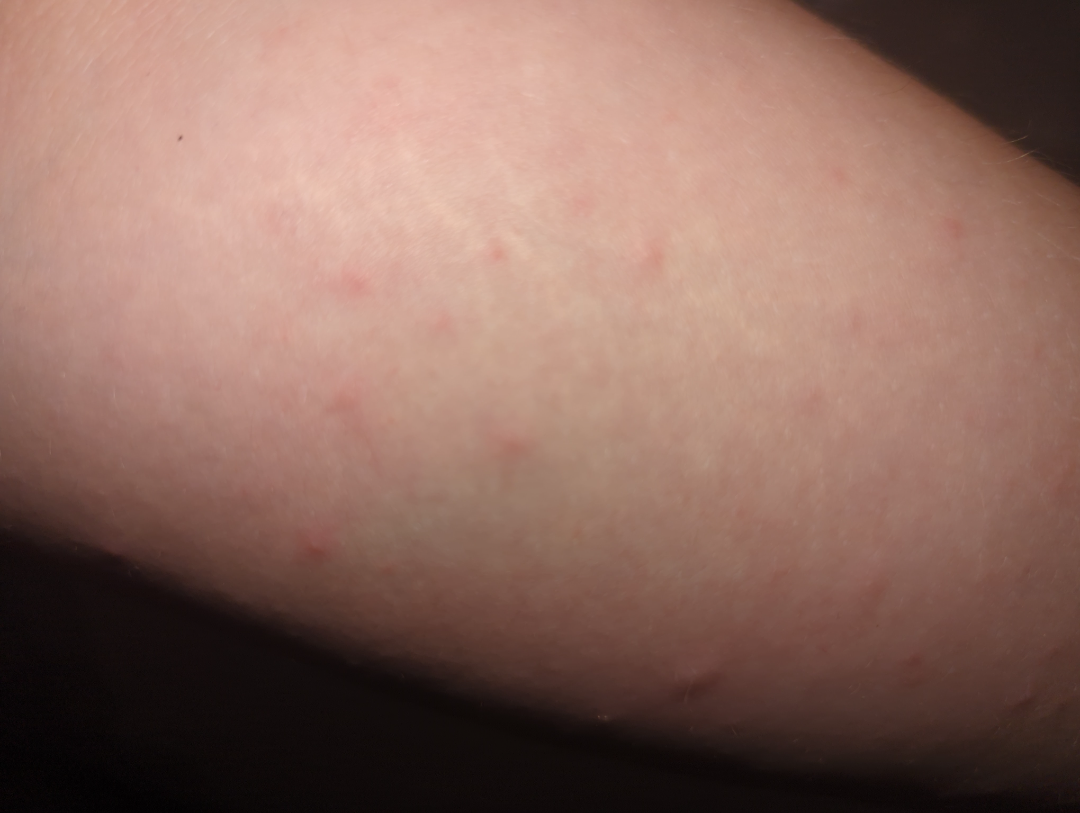assessment — not assessable | framing — close-up.